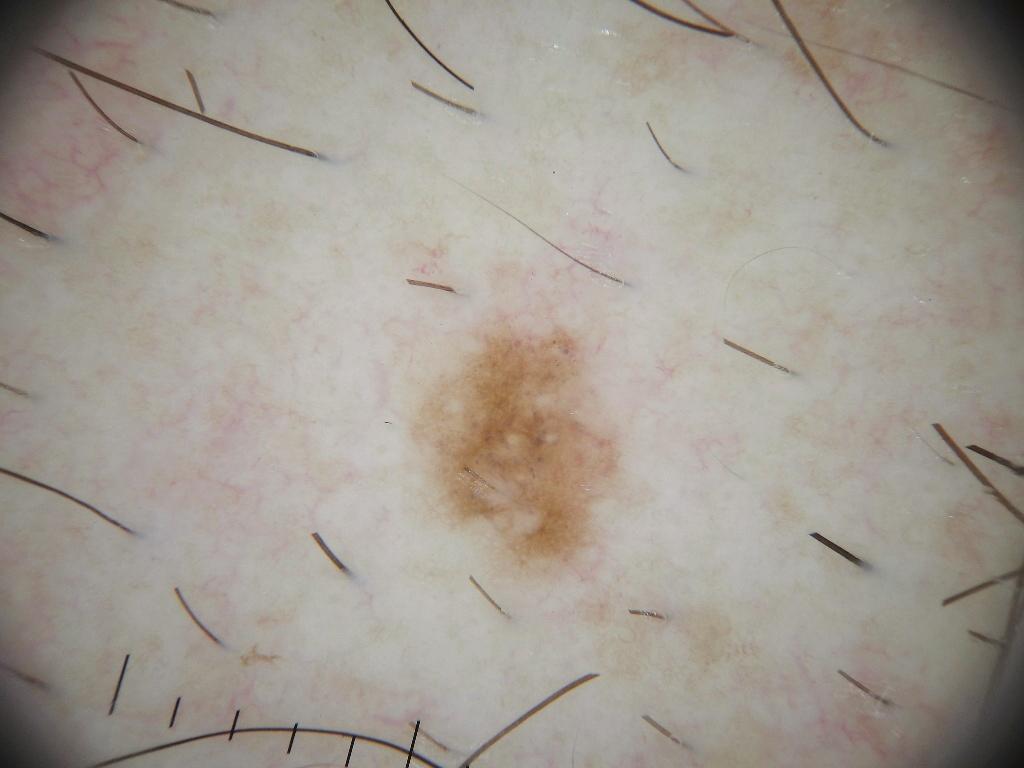Case summary: A dermoscopic close-up of a skin lesion. Dermoscopically, the lesion shows no pigment network, negative network, milia-like cysts, streaks, or globules. In (x1, y1, x2, y2) order, the visible lesion spans 413 316 619 579. Impression: Clinically diagnosed as a melanocytic nevus, a benign skin lesion.